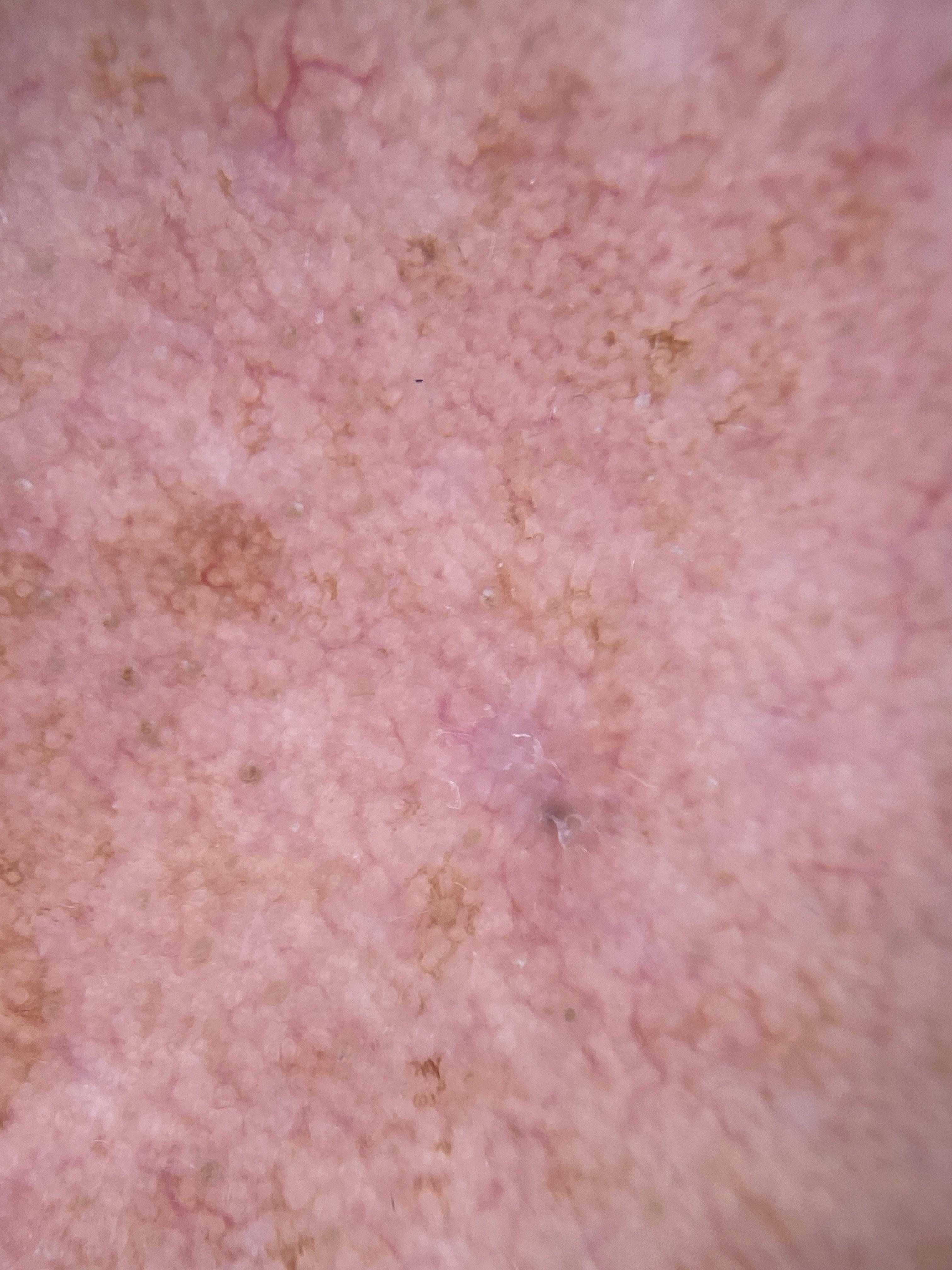| feature | finding |
|---|---|
| diagnosis | Nevus (biopsy-proven) |